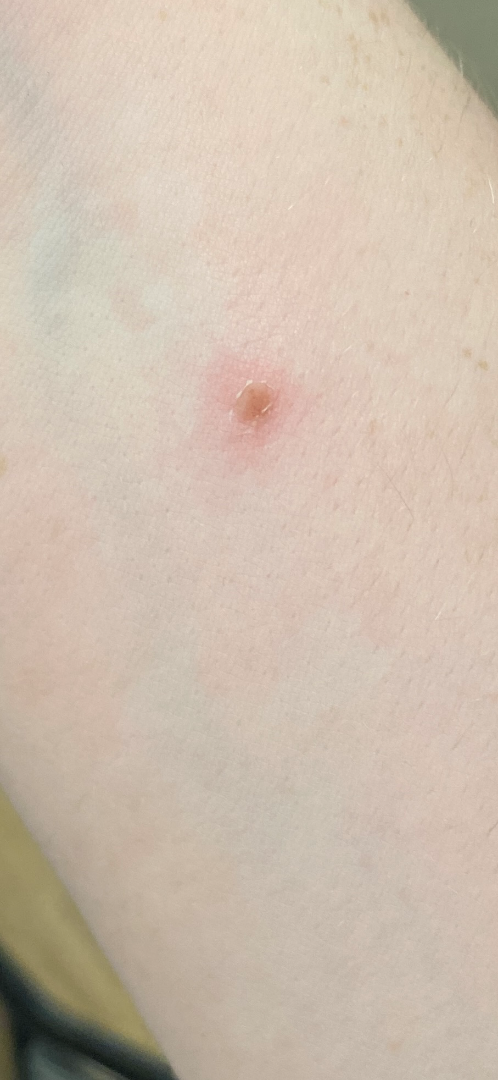affected area: arm | photo taken: close-up | symptoms: pain | present for: about one day | patient's own categorization: acne | subject: female, age 18–29 | differential diagnosis: Impetigo (possible); Insect Bite (possible).